A male patient aged around 35 — 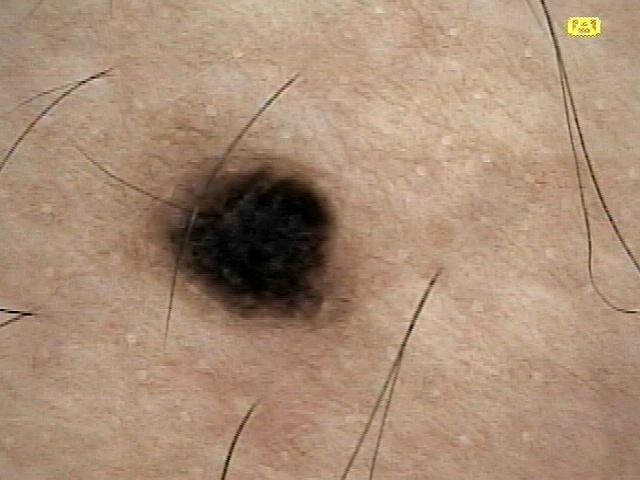{
  "diagnosis": {
    "name": "Nevus",
    "malignancy": "benign",
    "confirmation": "expert clinical impression",
    "lineage": "melanocytic"
  }
}